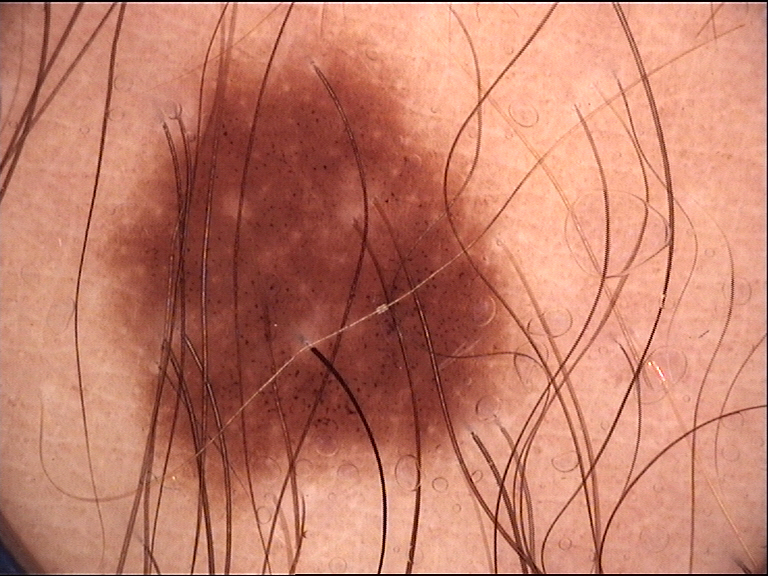A dermoscopy image of a single skin lesion. The diagnostic label was a dysplastic junctional nevus.